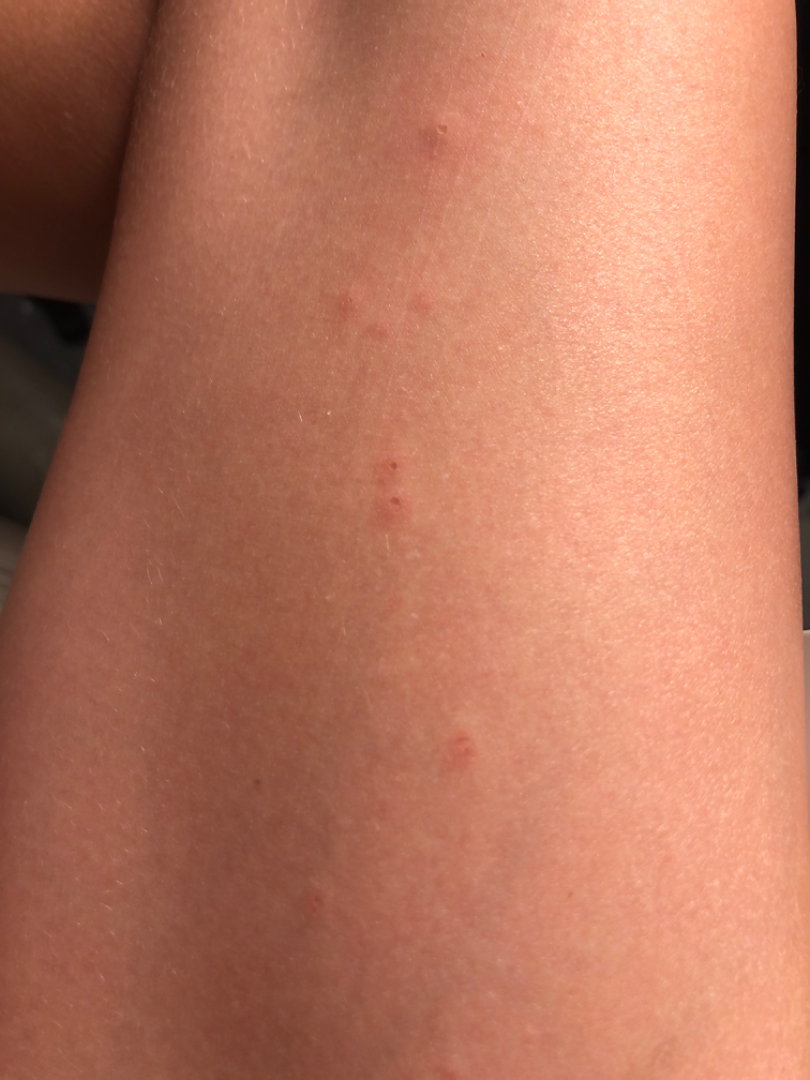This is a close-up image.
No relevant systemic symptoms.
Self-categorized by the patient as a rash.
The contributor notes the lesion is raised or bumpy.
Fitzpatrick phototype IV.
The patient is female.
The leg is involved.
Reported duration is about one day.
Symptoms reported: burning, pain and itching.
On dermatologist assessment of the image: the leading impression is Insect Bite; also consider Molluscum Contagiosum; an alternative is Allergic Contact Dermatitis; a more distant consideration is Urticaria.